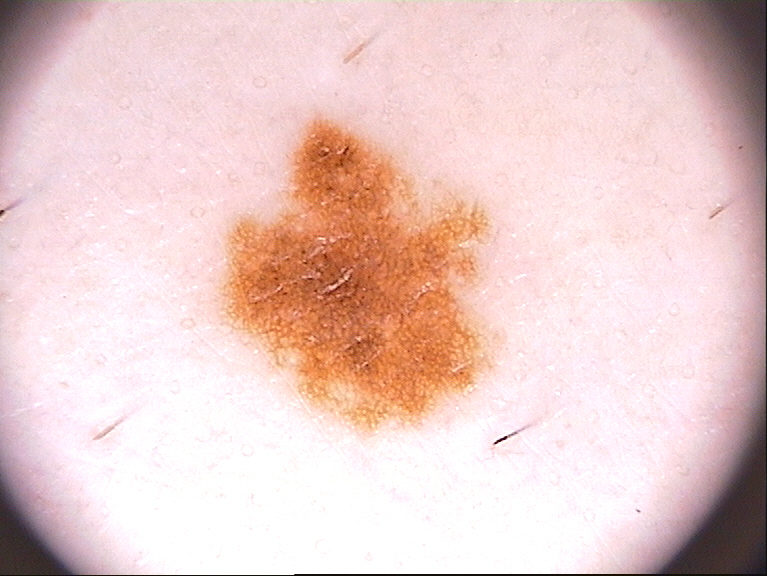patient — male, aged 13-17 | imaging — dermoscopy of a skin lesion | dermoscopic findings — pigment network and globules; absent: negative network, milia-like cysts, and streaks | lesion location — <box>213, 106, 497, 429</box> | assessment — a melanocytic nevus.